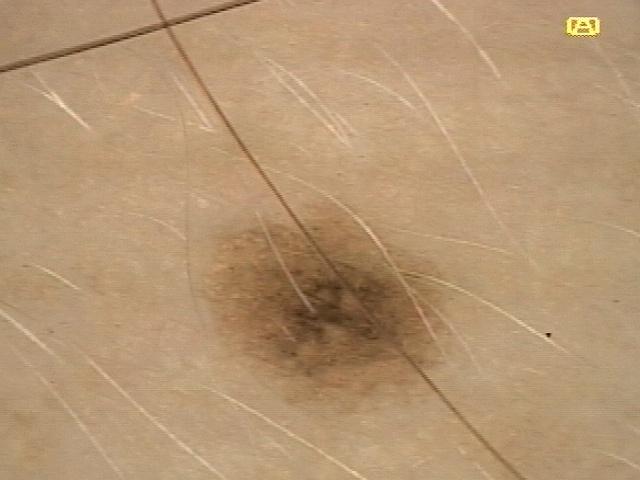Recorded as Fitzpatrick phototype II. A skin lesion imaged with a dermatoscope. The lesion was found on the trunk (the posterior trunk). Expert review favored a lesion of melanocytic origin — a nevus.